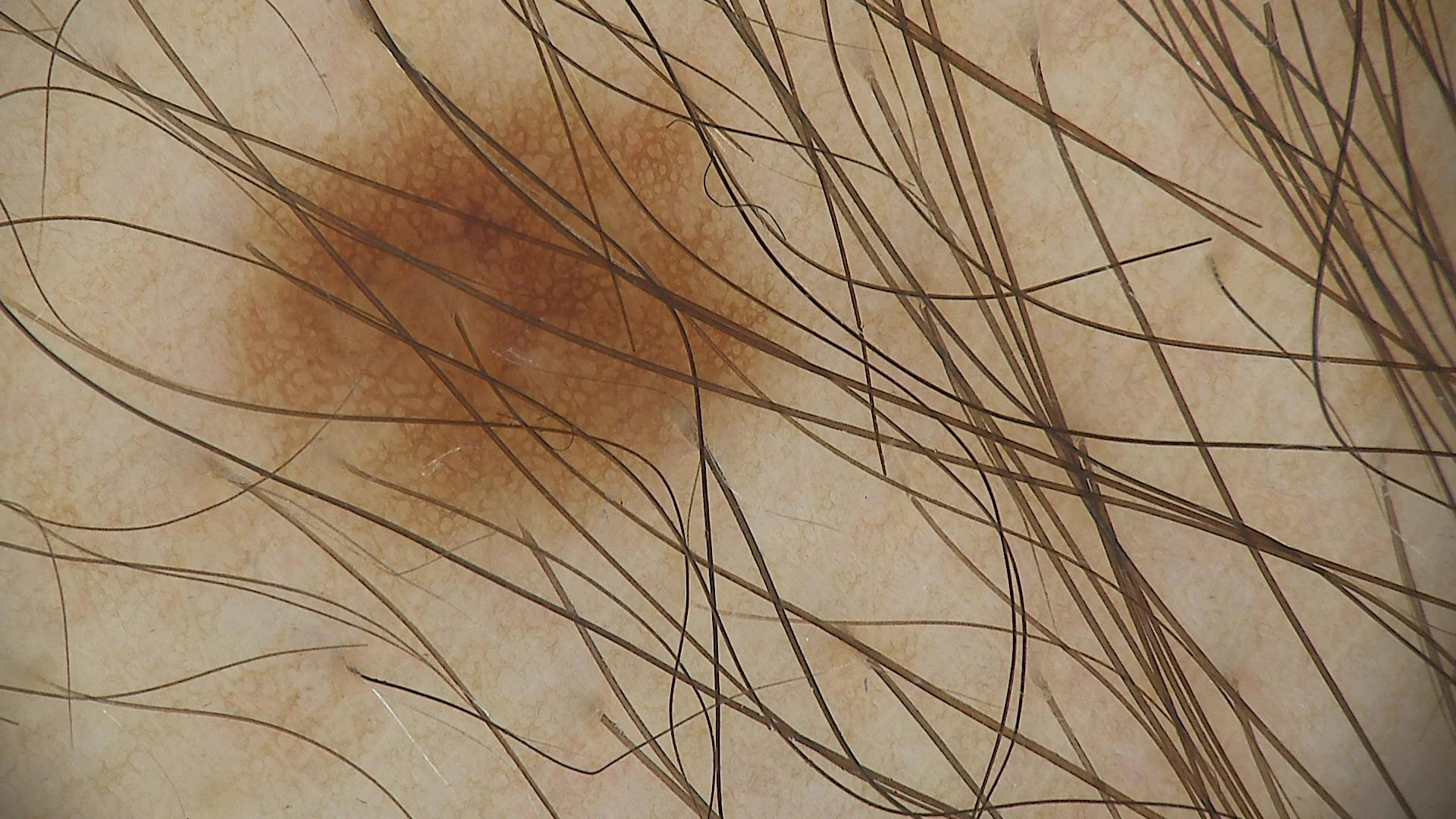{
  "diagnosis": {
    "name": "junctional nevus",
    "code": "jb",
    "malignancy": "benign",
    "super_class": "melanocytic",
    "confirmation": "expert consensus"
  }
}